The photograph is a close-up of the affected area. The condition has been present for less than one week. Texture is reported as raised or bumpy. The affected area is the head or neck and front of the torso. Reported lesion symptoms include itching: 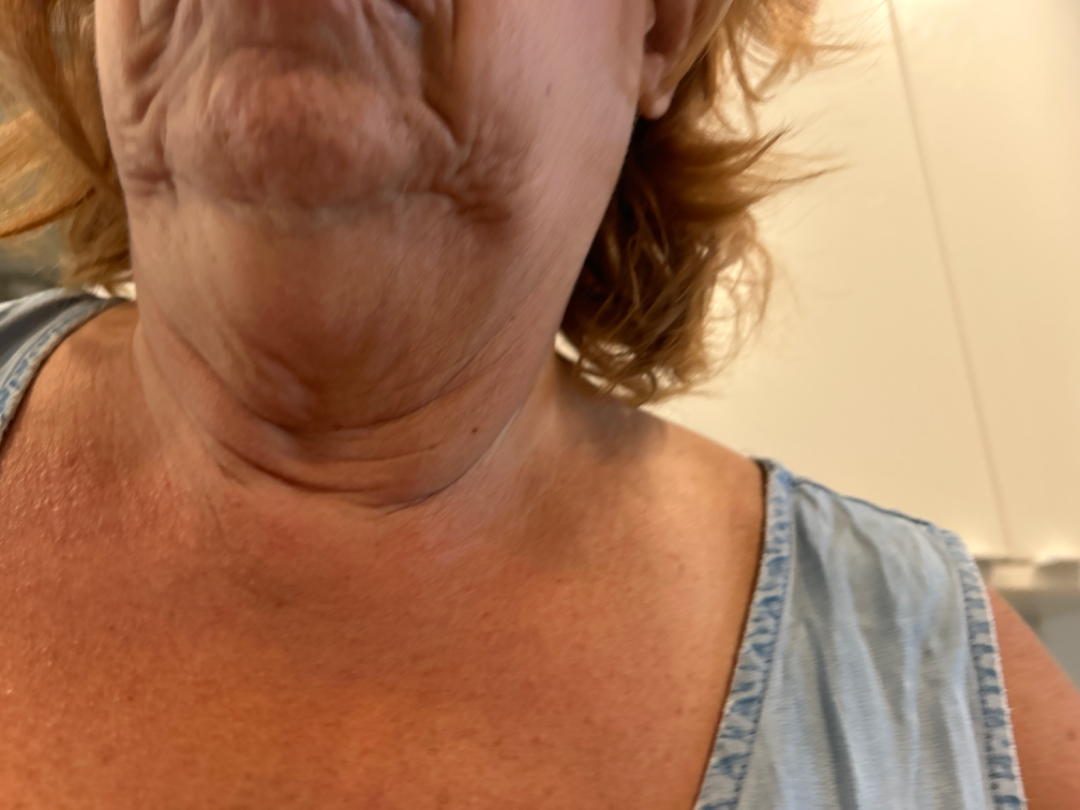Review:
The condition could not be reliably identified from the image.